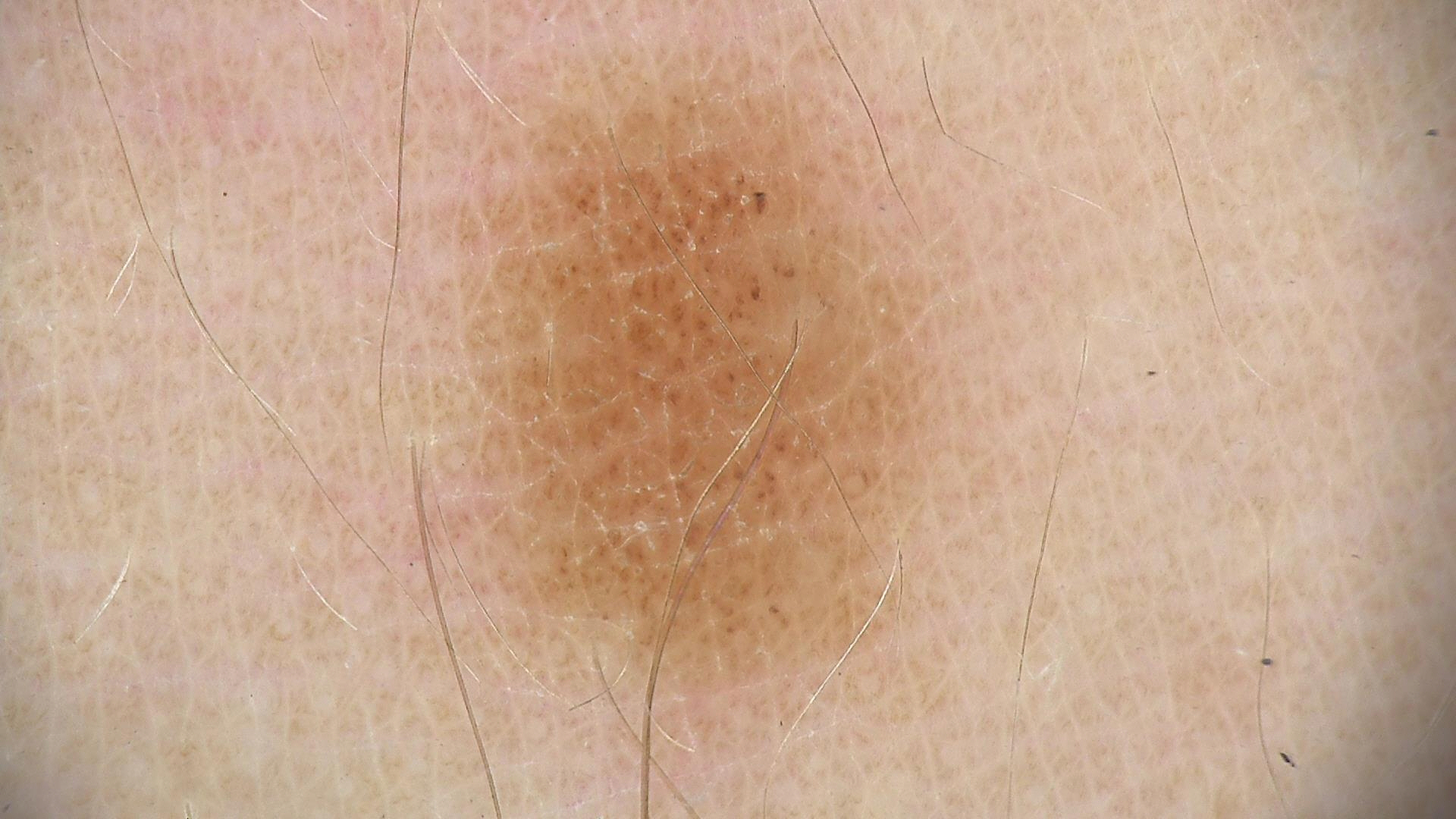Classified as a dysplastic junctional nevus.